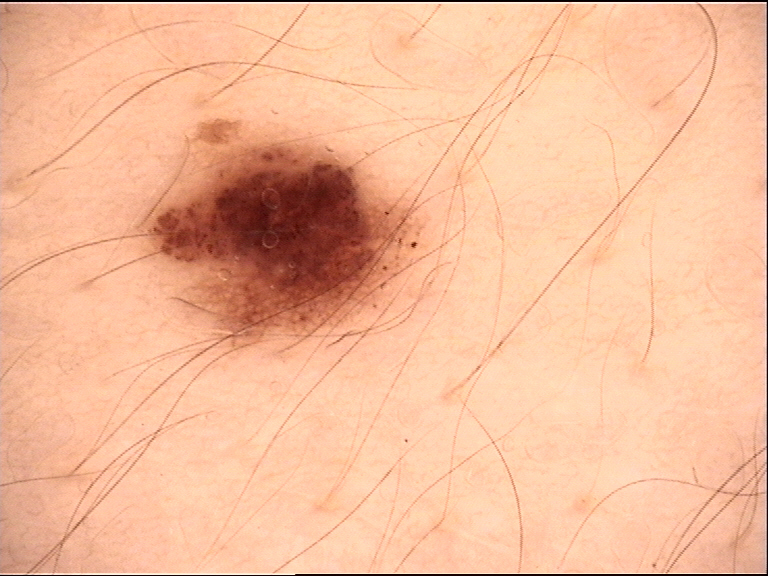{
  "image": "dermoscopy",
  "lesion_type": {
    "main_class": "banal",
    "pattern": "compound"
  },
  "diagnosis": {
    "name": "compound nevus",
    "code": "cb",
    "malignancy": "benign",
    "super_class": "melanocytic",
    "confirmation": "expert consensus"
  }
}